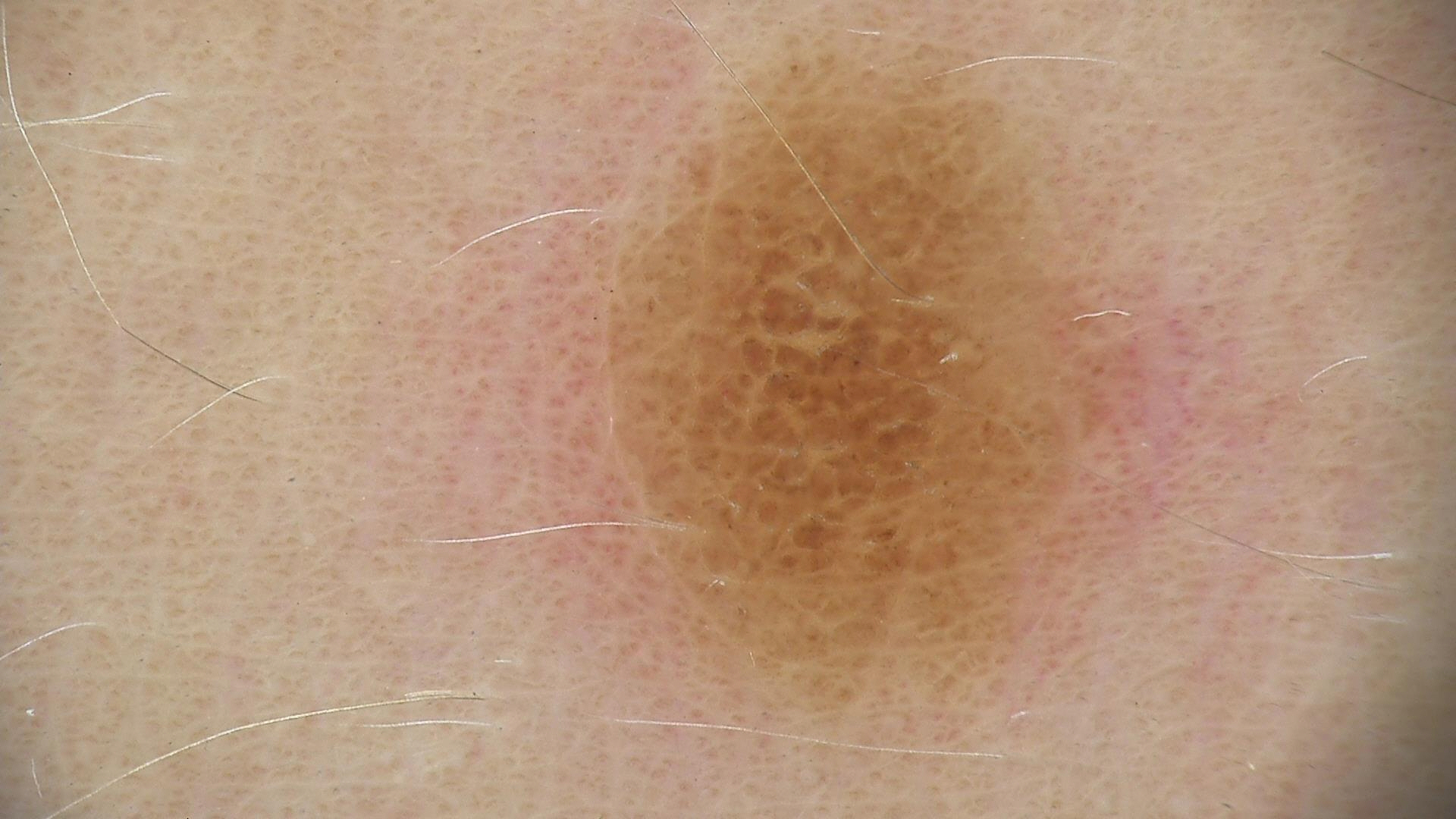A dermoscopy image of a single skin lesion. Consistent with a benign lesion — a dysplastic compound nevus.